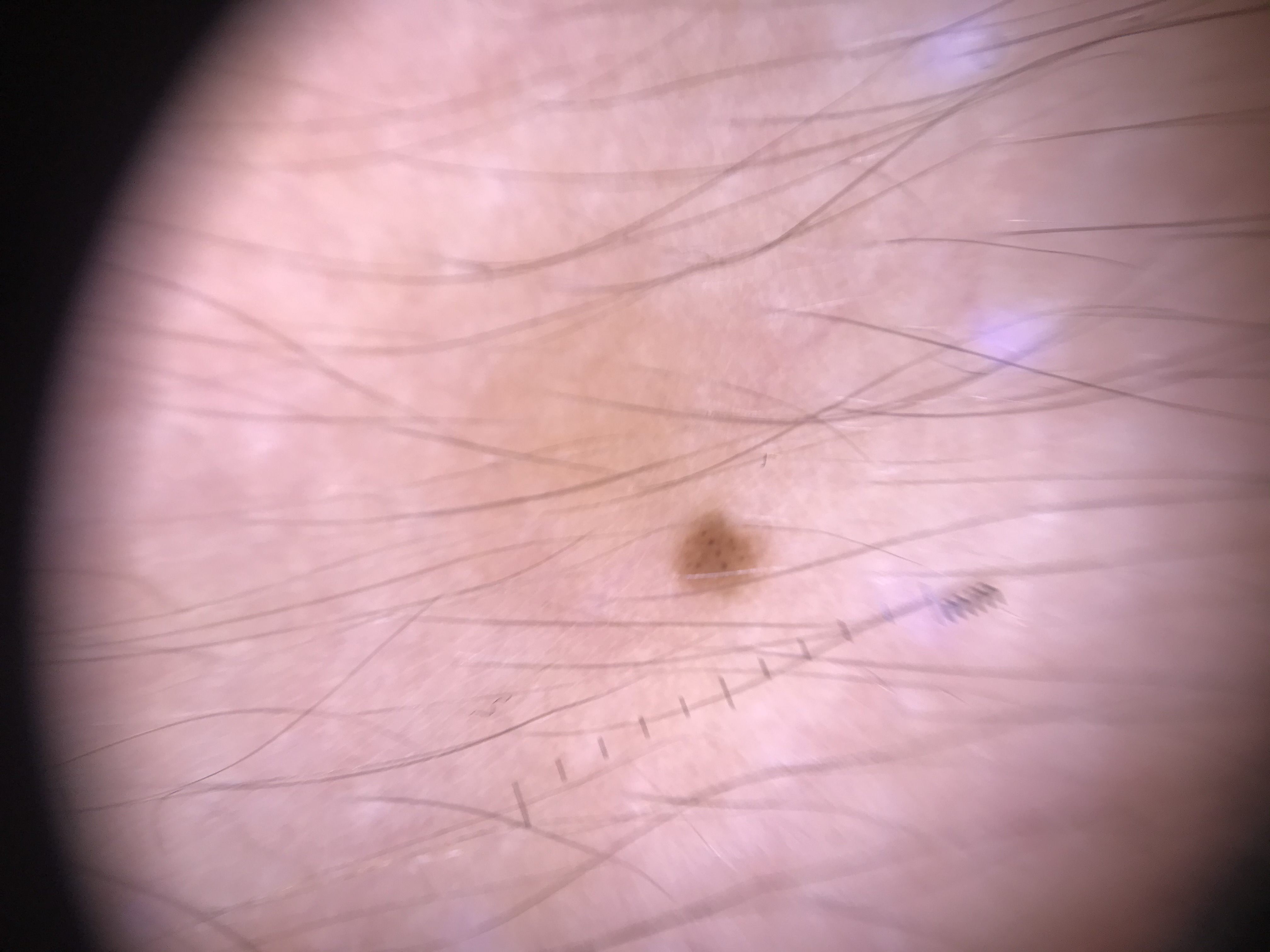diagnostic label: junctional nevus (expert consensus).